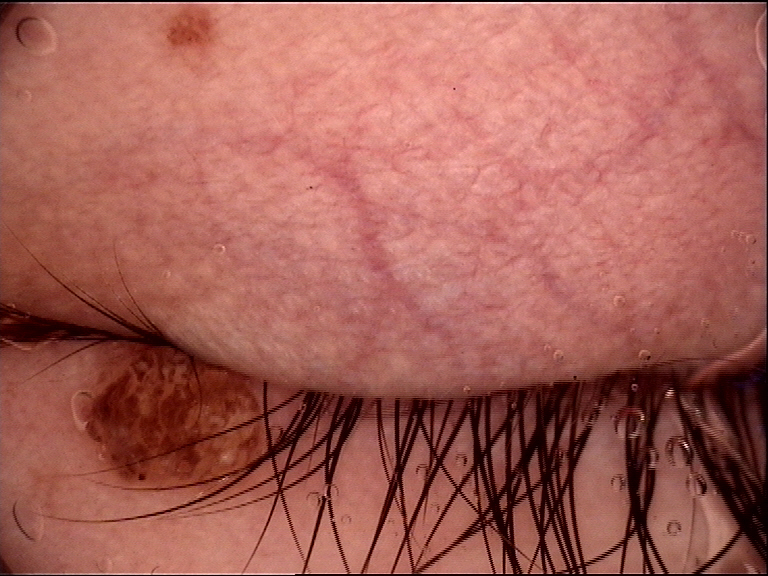A skin lesion imaged with a dermatoscope.
Labeled as a banal lesion — a congenital compound nevus.